A dermoscopic close-up of a skin lesion:
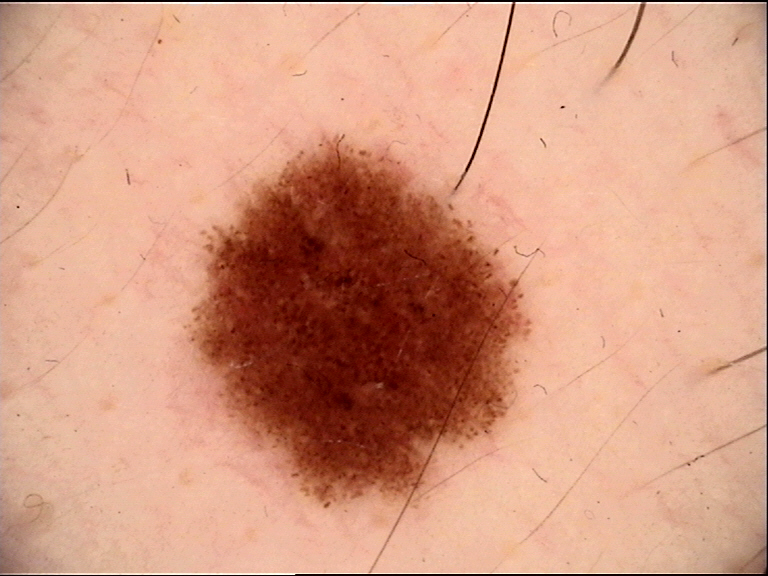Conclusion:
Diagnosed as a benign lesion — a dysplastic junctional nevus.